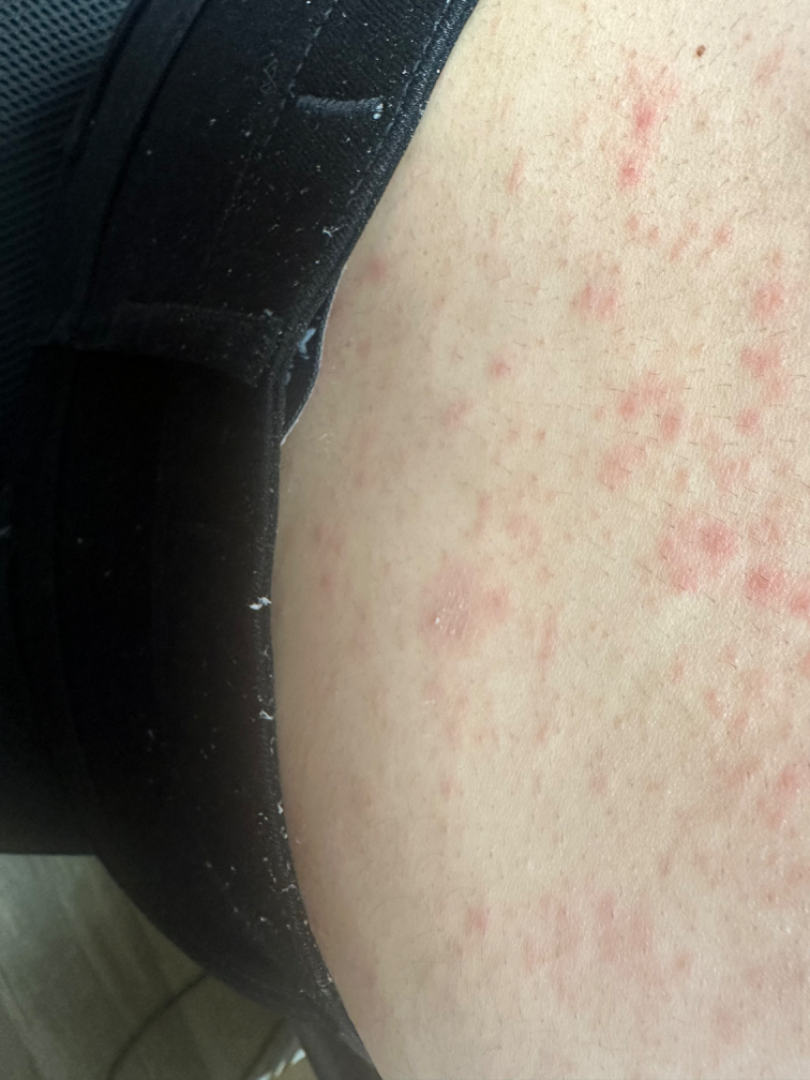shot type=close-up | subject=female, age 18–29 | clinical impression=Folliculitis (possible); Pityriasis rosea (possible); Hypersensitivity (possible).